The subject is a female aged 73-77 · a dermoscopic close-up of a skin lesion — 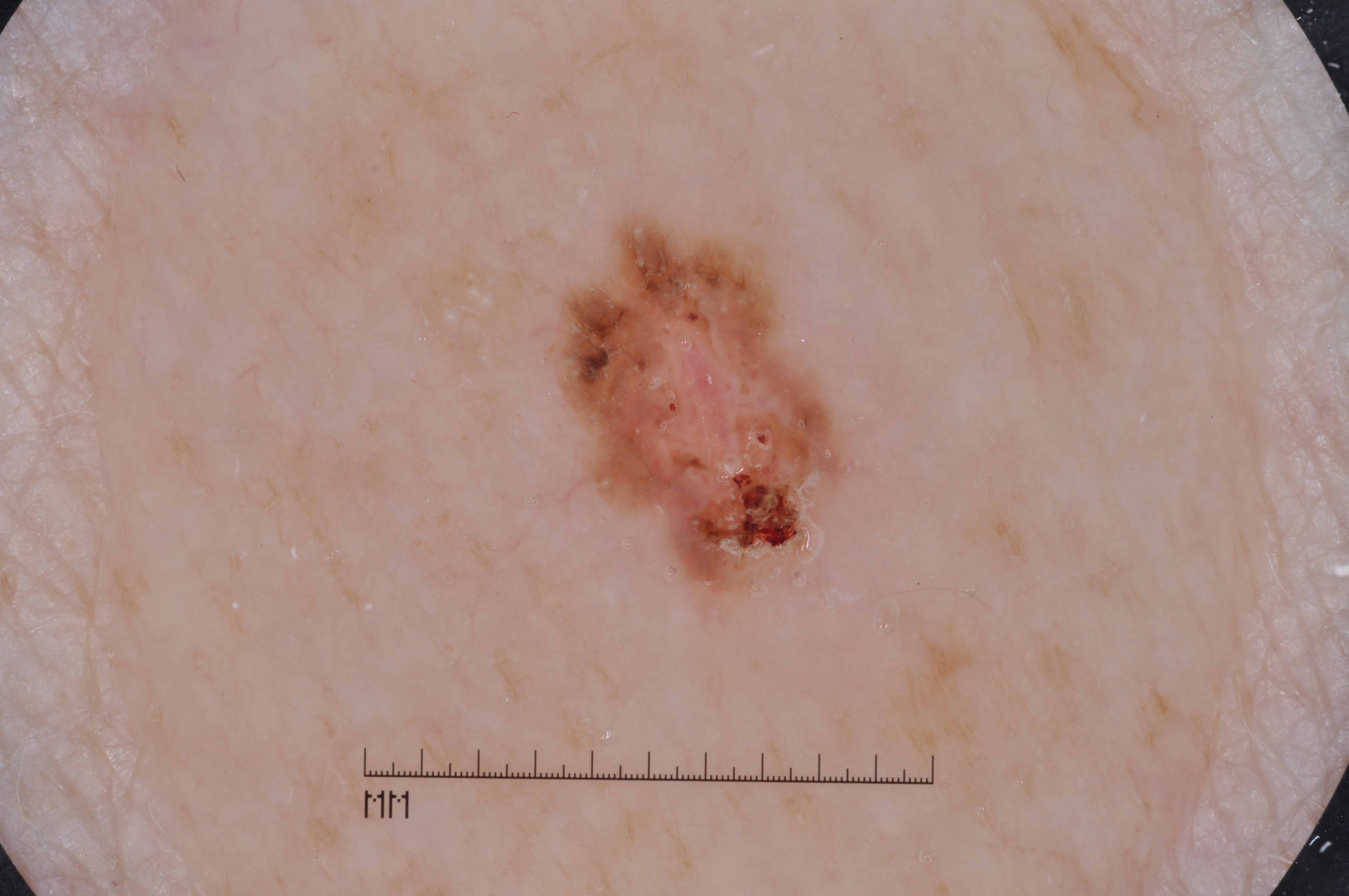Notes:
- location: x1=532 y1=204 x2=859 y2=629
- dermoscopic findings: milia-like cysts
- lesion size: small
- impression: a seborrheic keratosis